Close-up view:
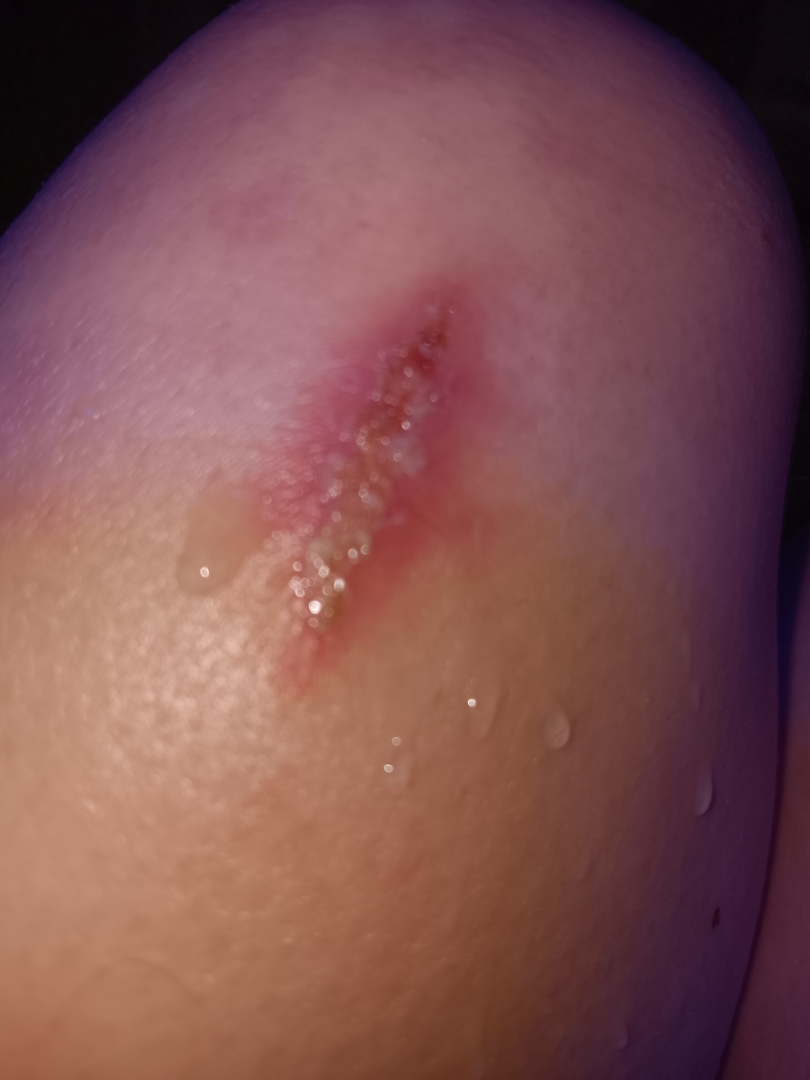Q: What is the differential diagnosis?
A: Allergic Contact Dermatitis (favored)